This is a close-up image — 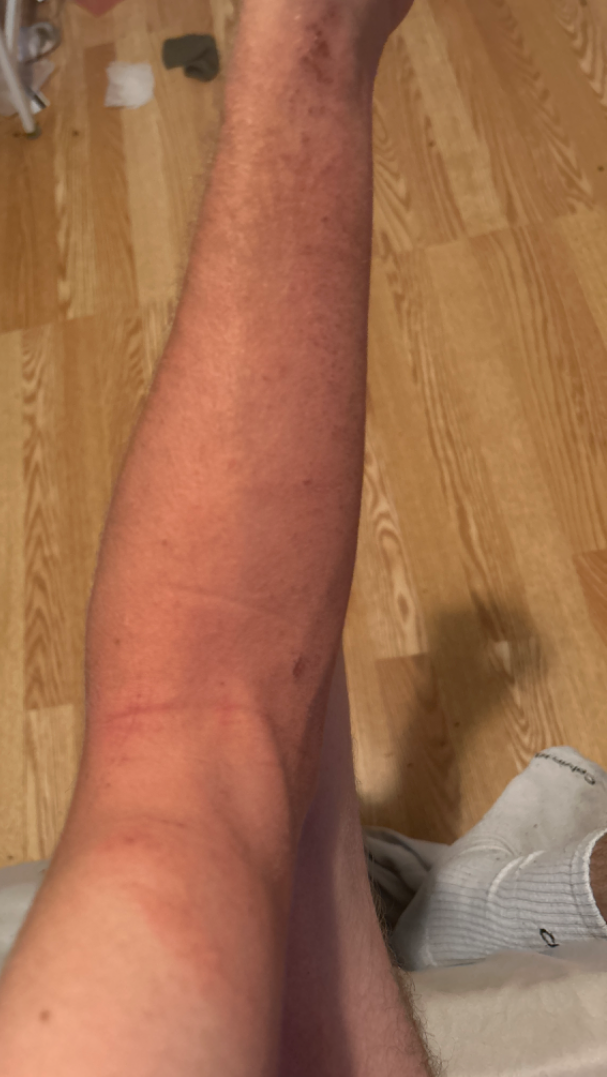| key | value |
|---|---|
| assessment | unable to determine |